A dermoscopic close-up of a skin lesion.
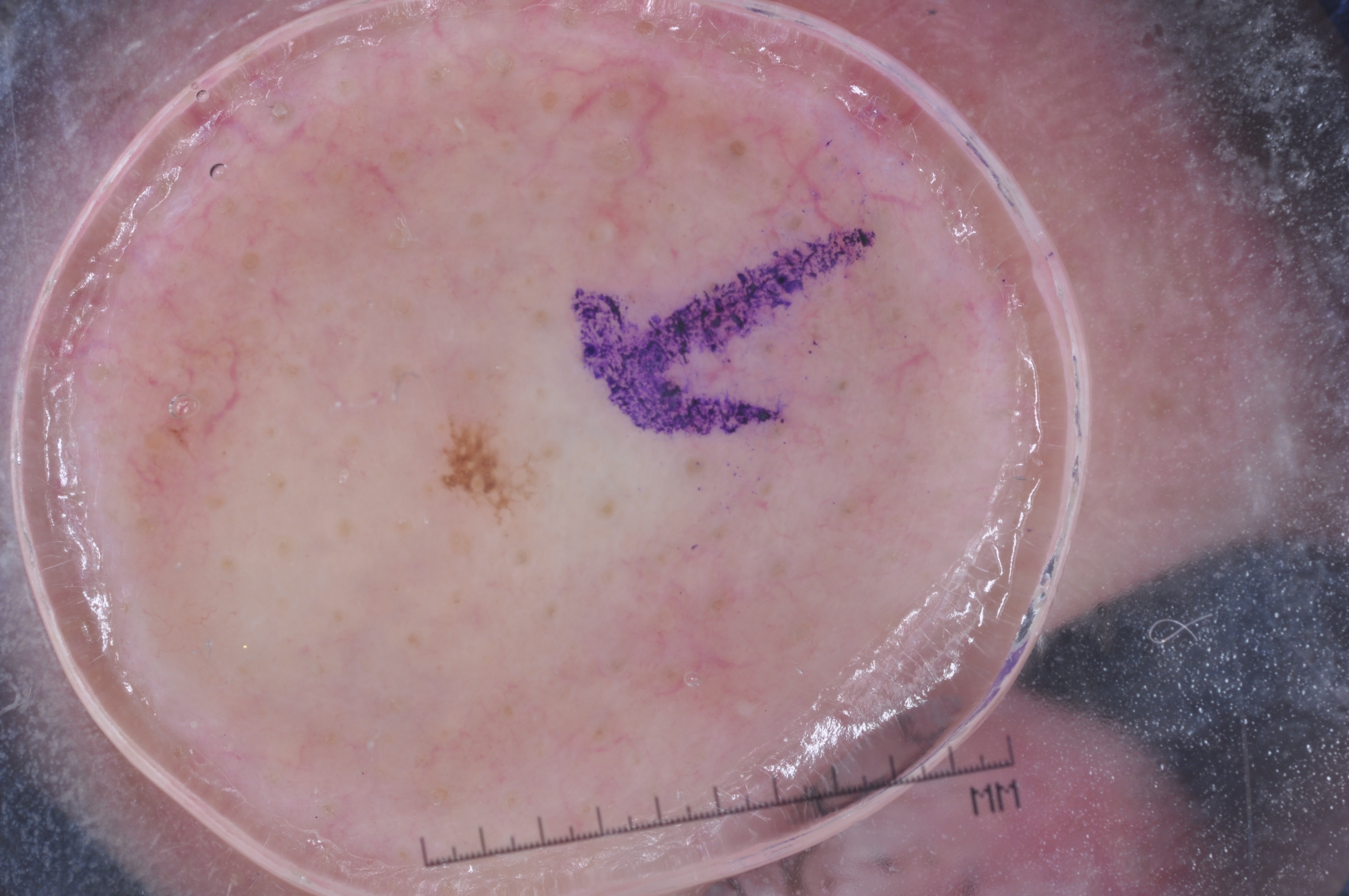The lesion is small relative to the field of view. Dermoscopic examination shows no pigment network, milia-like cysts, negative network, or streaks. Lesion location: <bbox>434, 412, 553, 535</bbox>. Diagnosed as a seborrheic keratosis, a keratinocytic lesion.